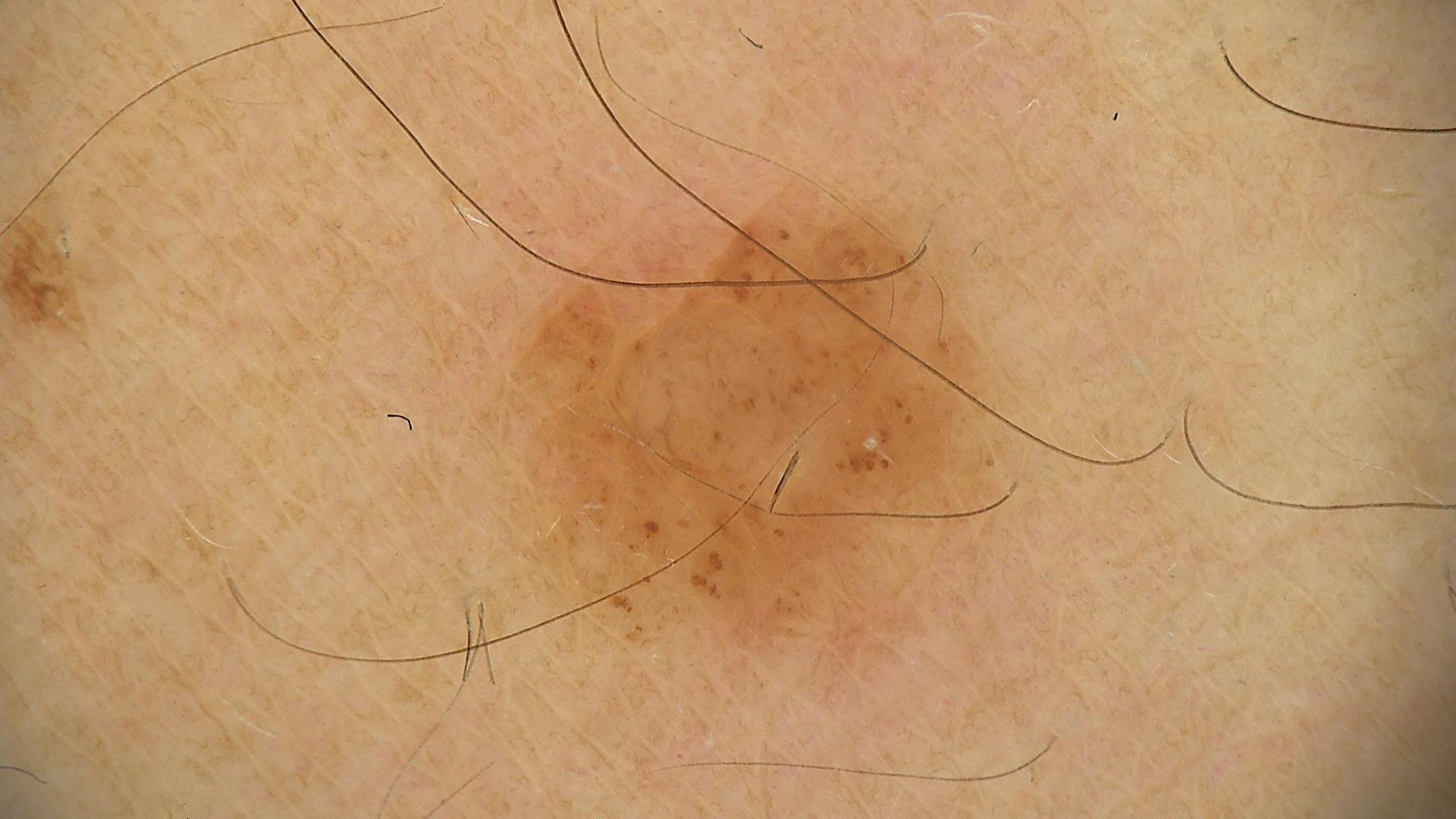Labeled as a compound nevus.